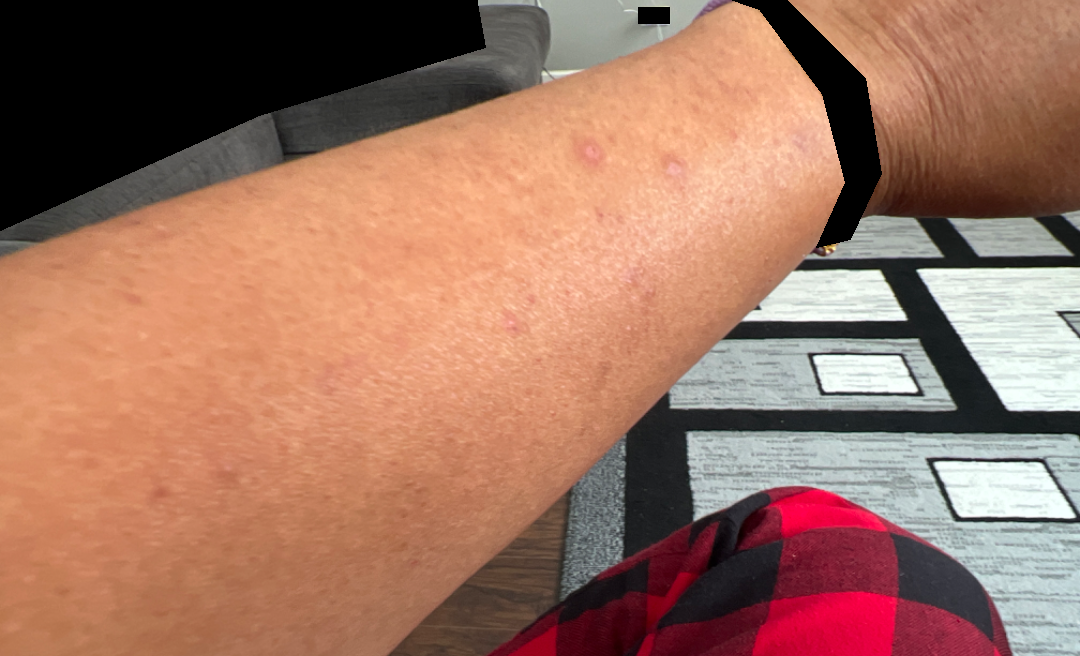| feature | finding |
|---|---|
| onset | three to twelve months |
| location | arm |
| subject | female |
| shot type | close-up |
| patient's own categorization | a rash |
| constitutional symptoms | chills, fatigue, joint pain and shortness of breath |
| symptoms | enlargement, bothersome appearance, darkening and itching |
| texture | rough or flaky and raised or bumpy |
| differential | most consistent with Prurigo nodularis |